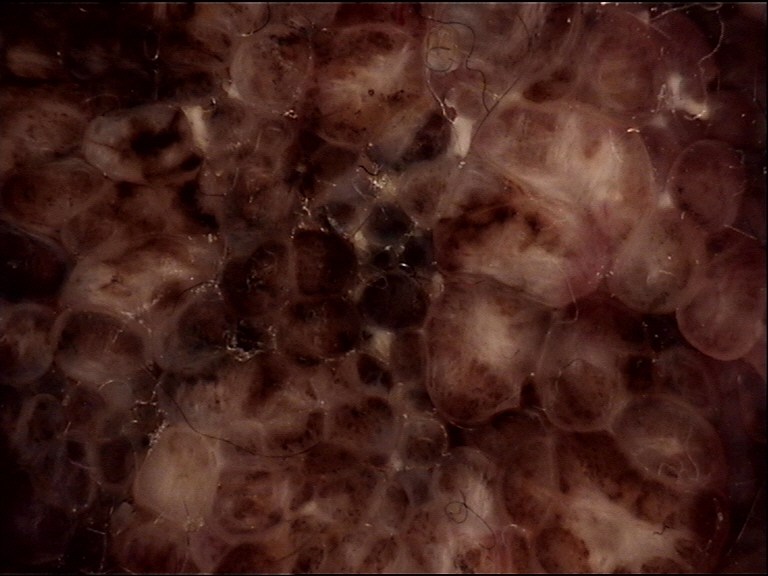Q: What kind of image is this?
A: dermatoscopy
Q: What is this lesion?
A: congenital compound nevus (expert consensus)